The patient is a male aged 18–29. This image was taken at a distance. The affected area is the arm and back of the hand:
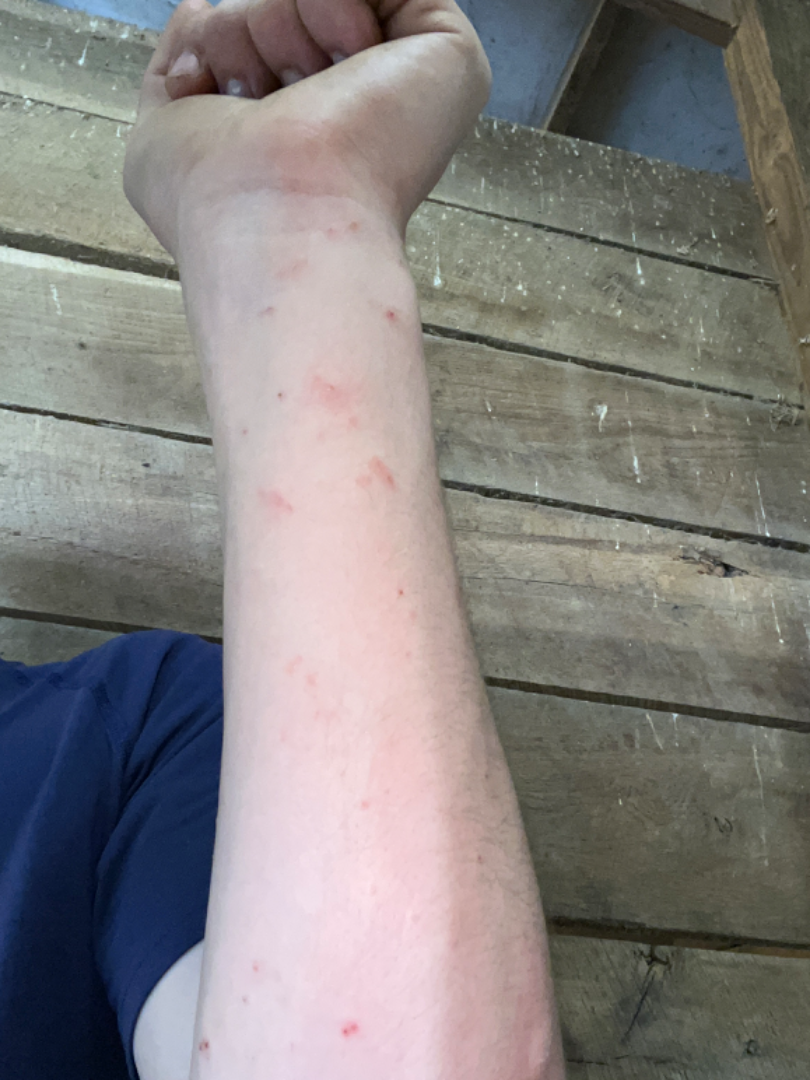assessment: indeterminate